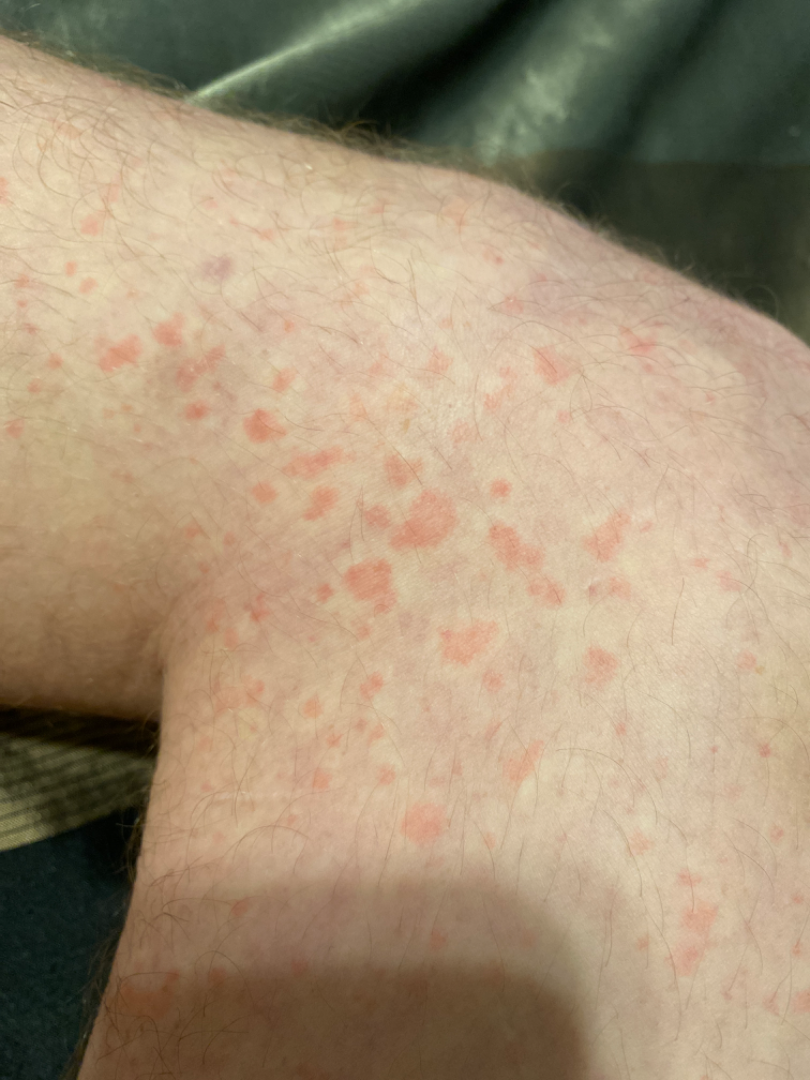The lesion involves the leg.
Close-up view.
Favoring Urticaria; also raised was Leukocytoclastic Vasculitis.